A dermoscopic photograph of a skin lesion.
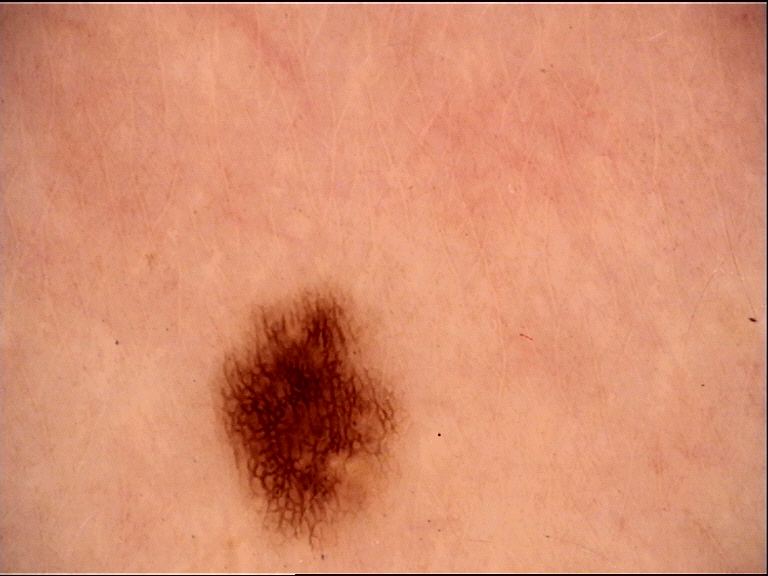diagnosis = dysplastic junctional nevus (expert consensus).